A clinical photograph showing a skin lesion. A female subject in their late 50s:
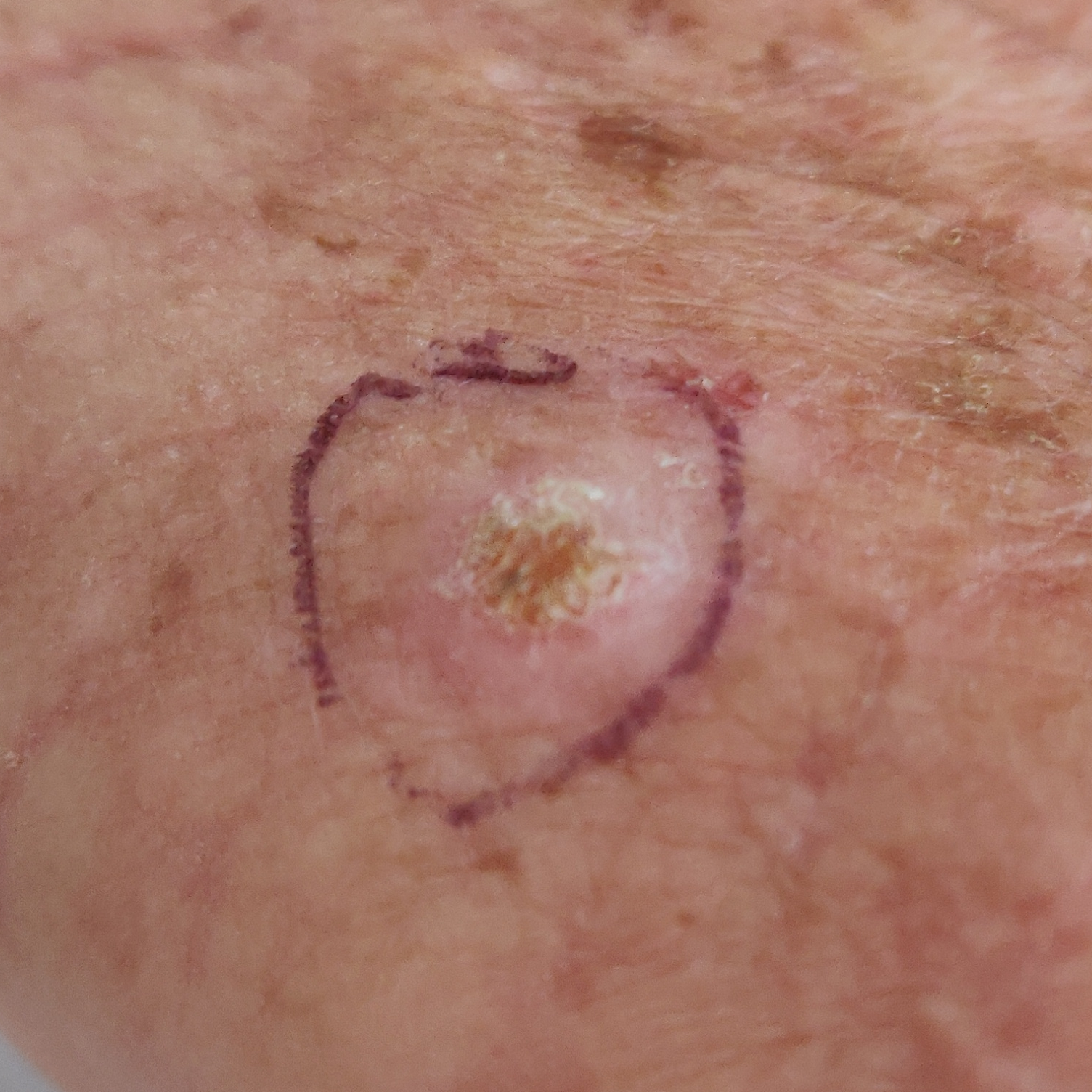  lesion_location: a hand
  symptoms:
    present:
      - elevation
      - growth
      - itching
    absent:
      - bleeding
  diagnosis:
    name: squamous cell carcinoma
    code: SCC
    malignancy: malignant
    confirmation: histopathology